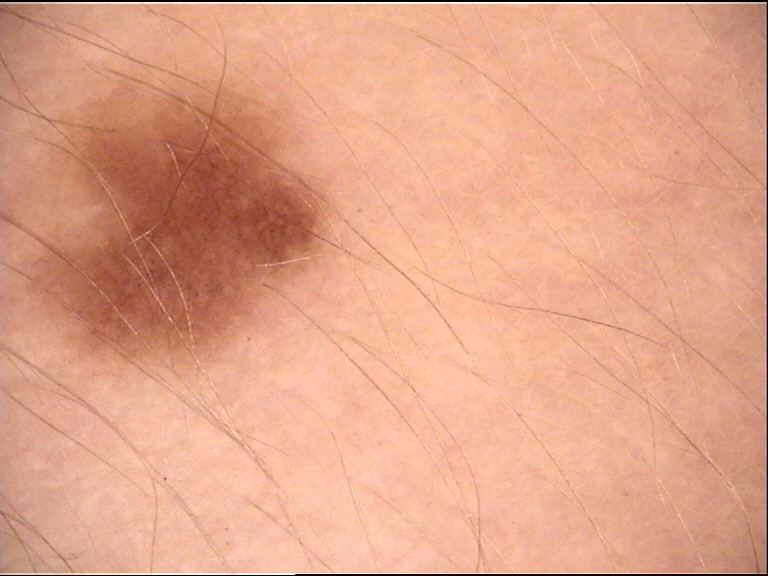A dermoscopic image of a skin lesion.
Labeled as a benign lesion — a dysplastic junctional nevus.